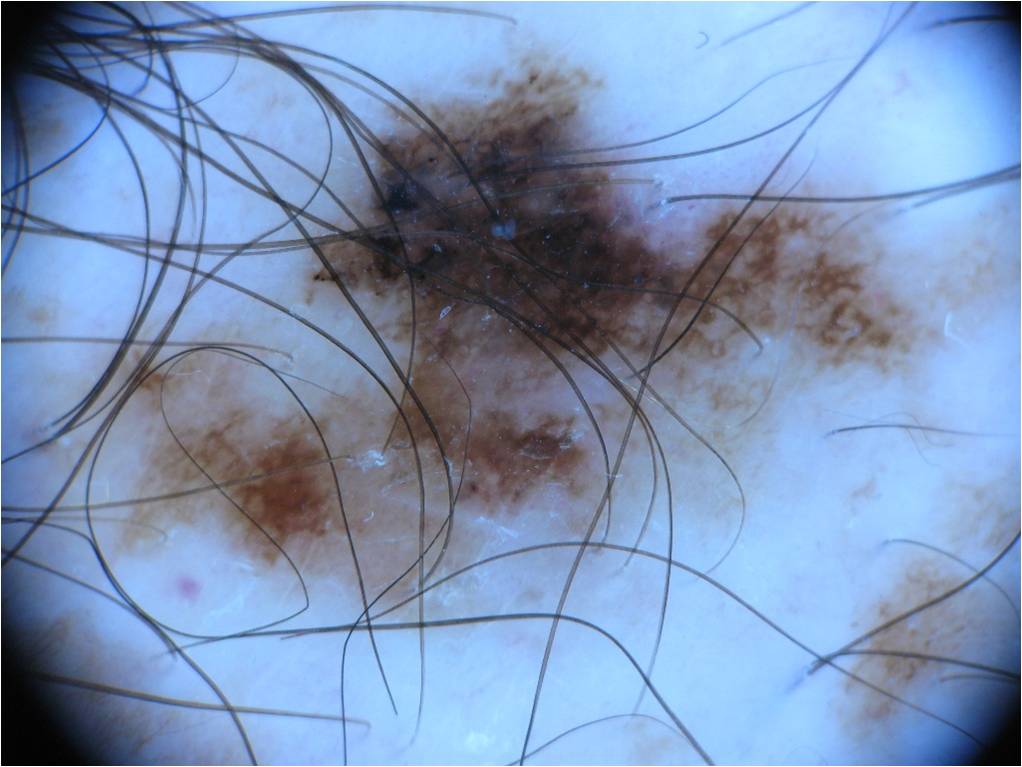Case summary:
A skin lesion imaged with a dermatoscope. A male patient, aged around 25. On dermoscopy, the lesion shows pigment network. The lesion spans x1=41 y1=51 x2=1013 y2=634.
Conclusion:
Biopsy-confirmed as a melanoma, a malignancy.